Dermoscopy of a skin lesion.
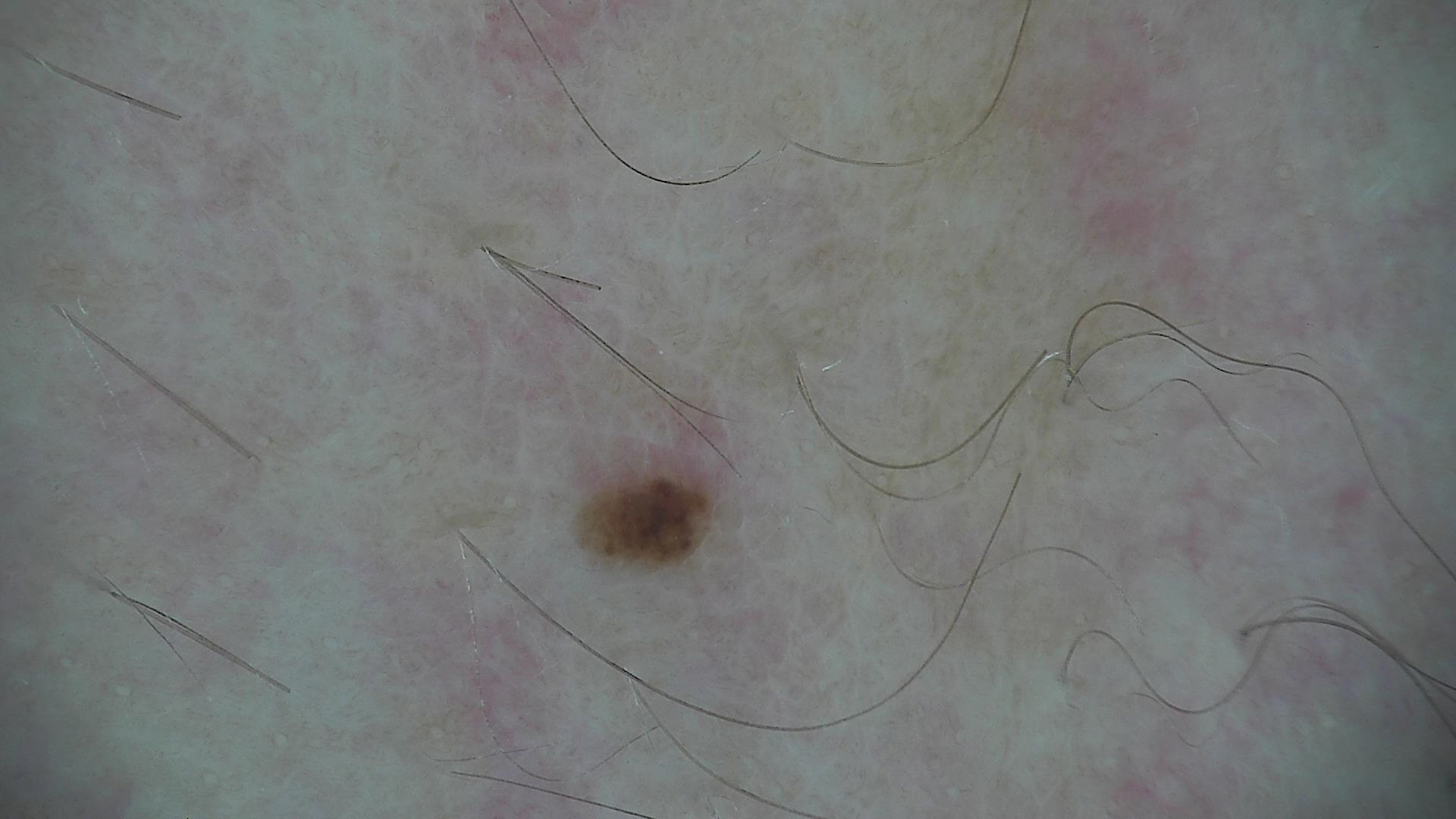{"diagnosis": {"name": "dysplastic junctional nevus", "code": "jd", "malignancy": "benign", "super_class": "melanocytic", "confirmation": "expert consensus"}}